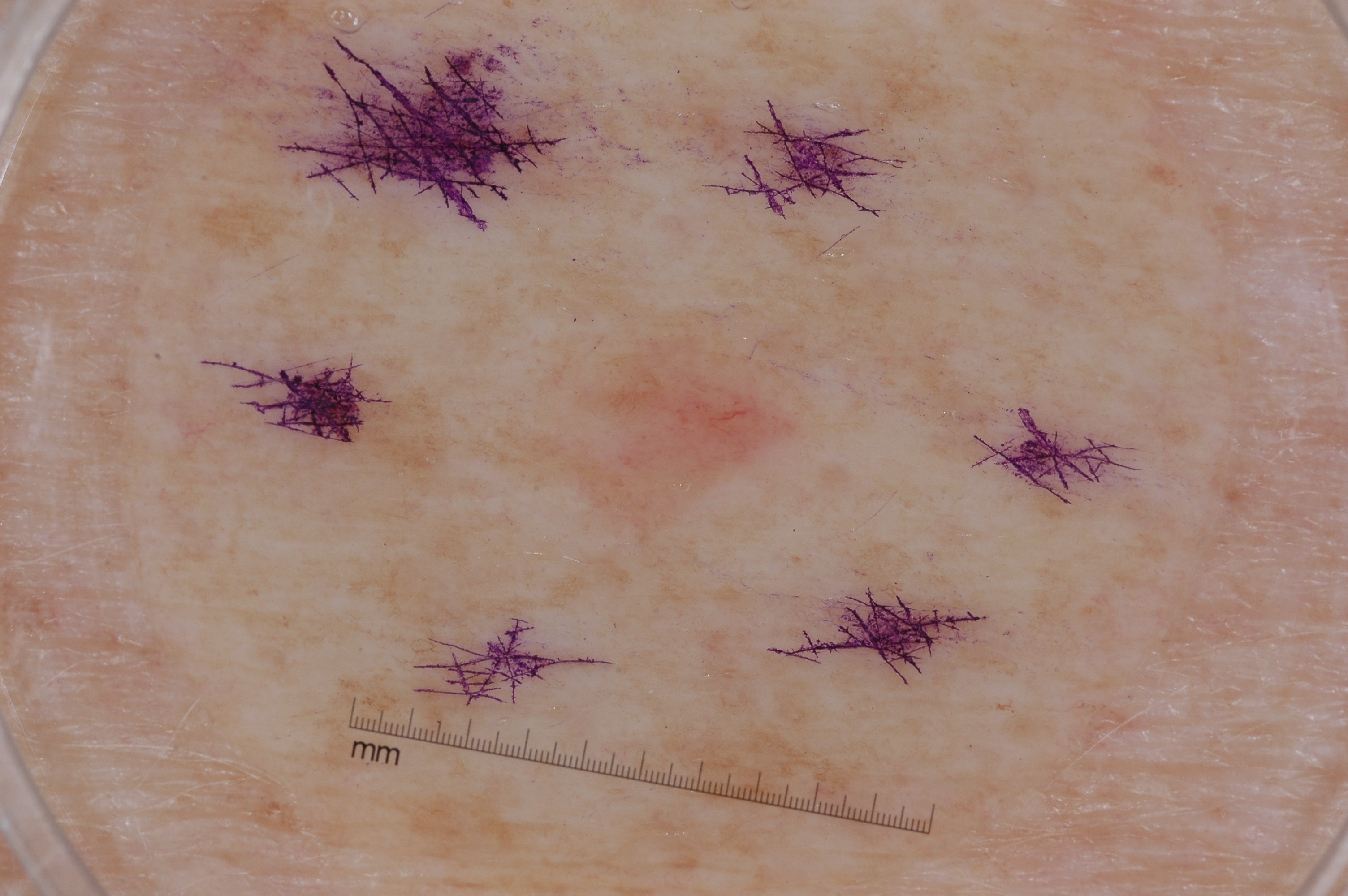A dermoscopic image of a skin lesion. Lesion location: left=441, top=217, right=899, bottom=610. The dermoscopic pattern shows no streaks, milia-like cysts, pigment network, or negative network. A mid-sized lesion within the field. Clinically diagnosed as a melanocytic nevus.